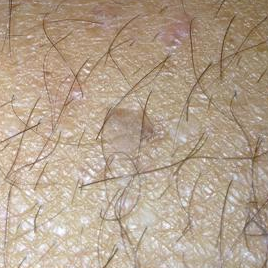| field | value |
|---|---|
| patient | in their 30s |
| image | clinical photograph |
| diagnostic label | seborrheic keratosis (clinical consensus) |